A dermoscopic photograph of a skin lesion: 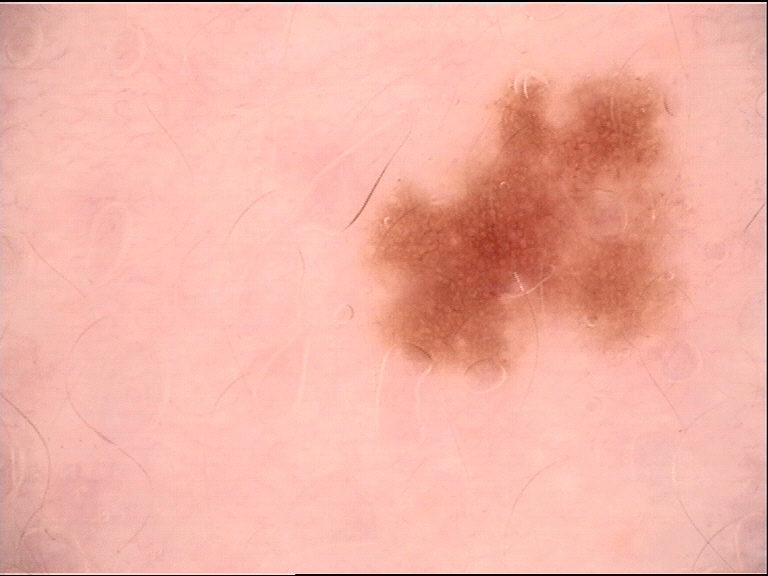Impression:
Consistent with a dysplastic junctional nevus.